A male subject about 15 years old; a skin lesion imaged with a dermatoscope.
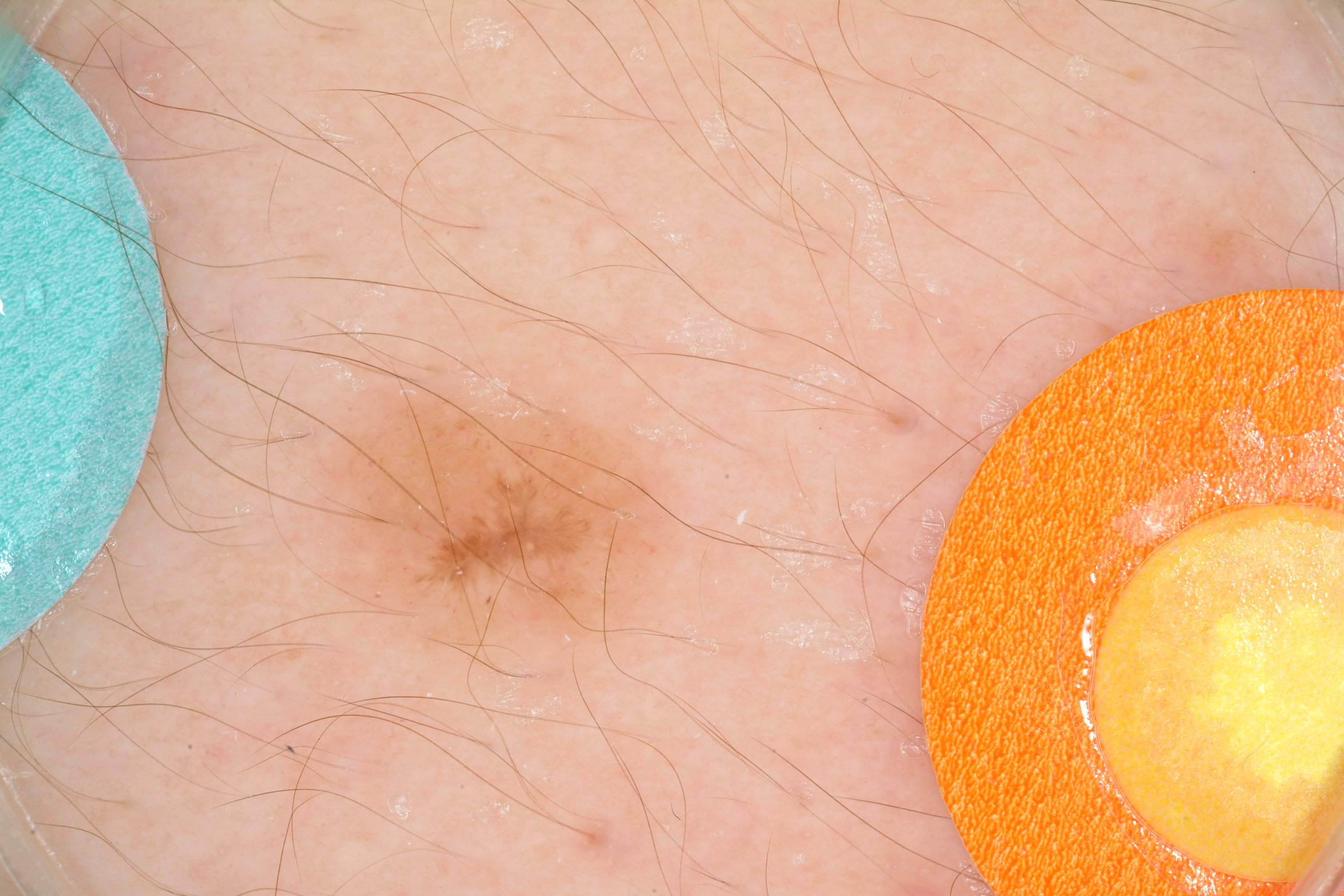In (x1, y1, x2, y2) order, lesion location: [326, 387, 661, 662]. The dermoscopic pattern shows no globules, pigment network, milia-like cysts, negative network, or streaks. The lesion was assessed as a melanocytic nevus, a benign lesion.